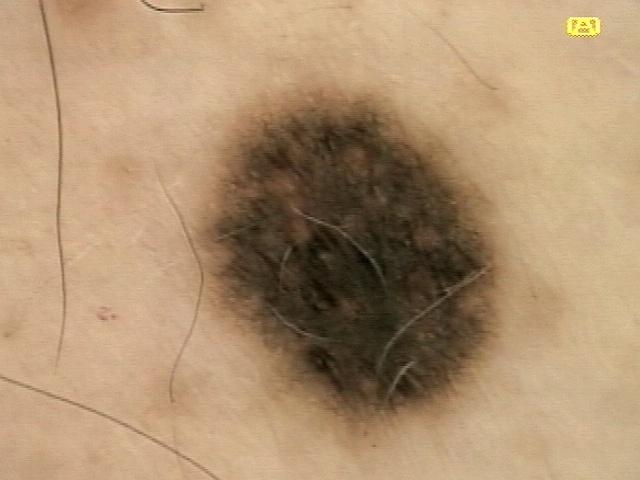diagnosis:
  name: Nevus
  malignancy: benign
  confirmation: histopathology
  lineage: melanocytic